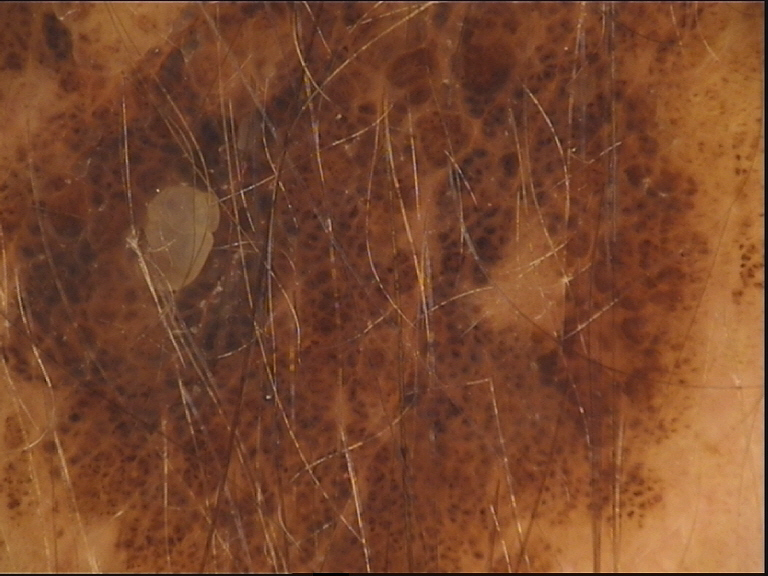The diagnostic label was a congenital compound nevus.